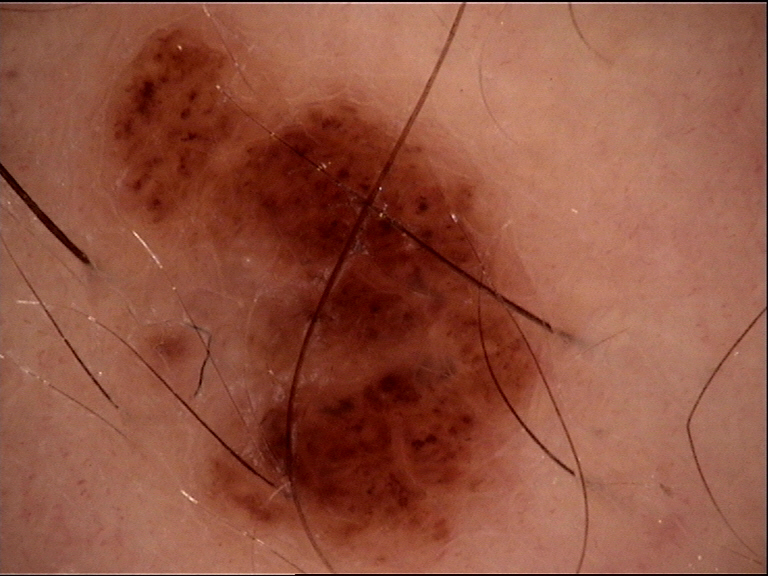image — dermatoscopy | diagnosis — compound nevus (expert consensus).